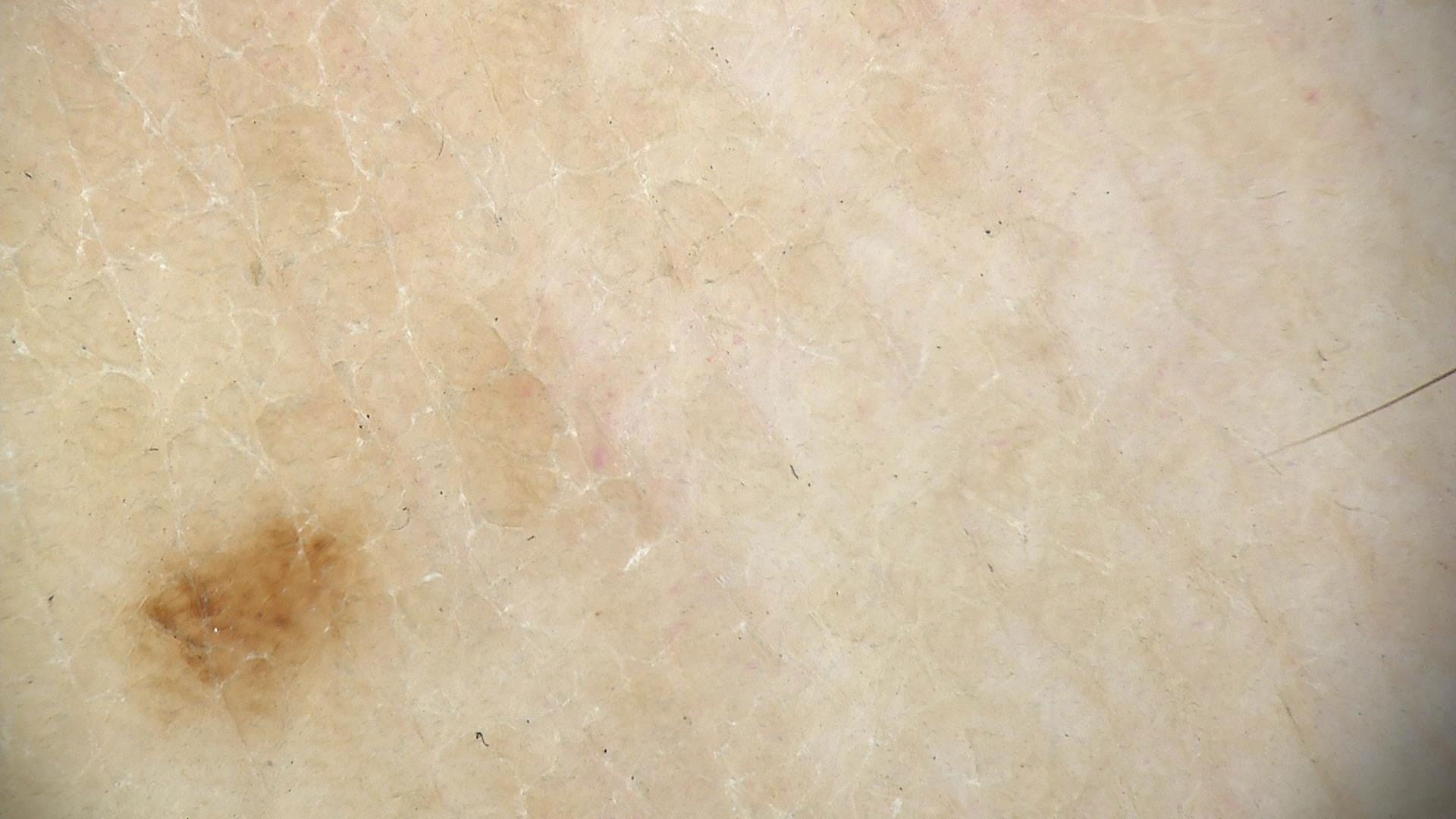Q: What was the diagnostic impression?
A: dysplastic junctional nevus (expert consensus)